A dermoscopy image of a single skin lesion.
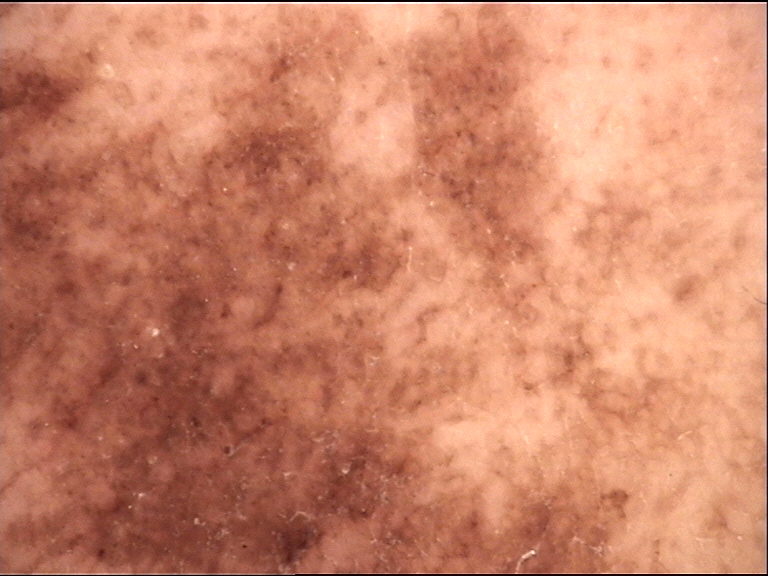The morphology is that of a banal lesion.
Labeled as a congenital compound nevus.